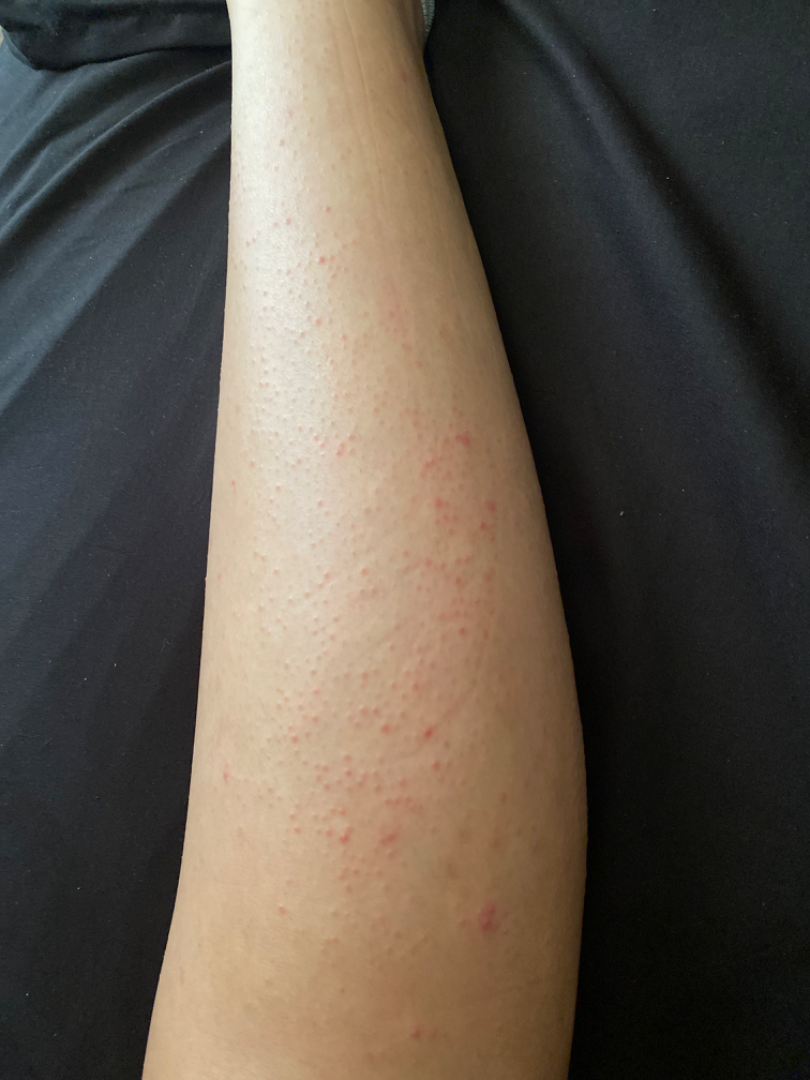shot type — at a distance | differential — Lichen nitidus (favored); Lichen planus/lichenoid eruption (possible); Molluscum Contagiosum (possible).